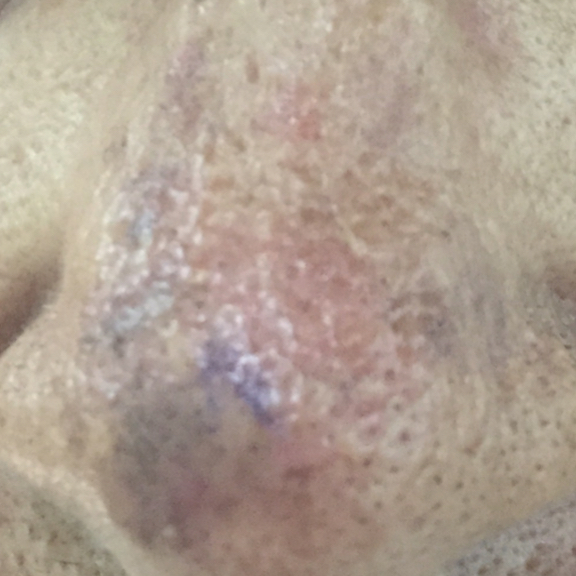Case:
• image · smartphone clinical photo
• subject · age 72
• body site · the nose
• reported symptoms · itching
• diagnosis · actinic keratosis (clinical consensus)